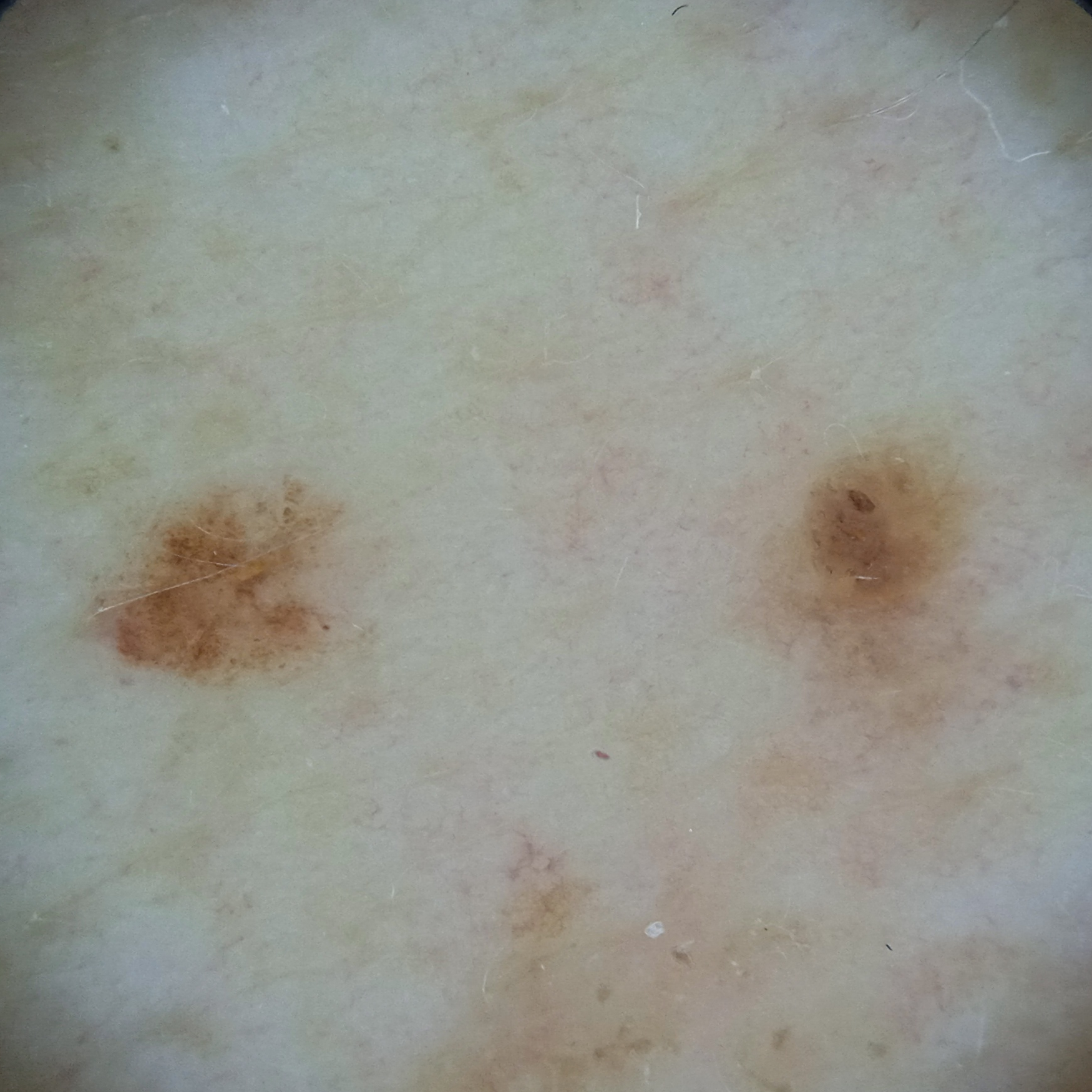Conclusion: The dermatologists' assessment was a seborrheic keratosis.